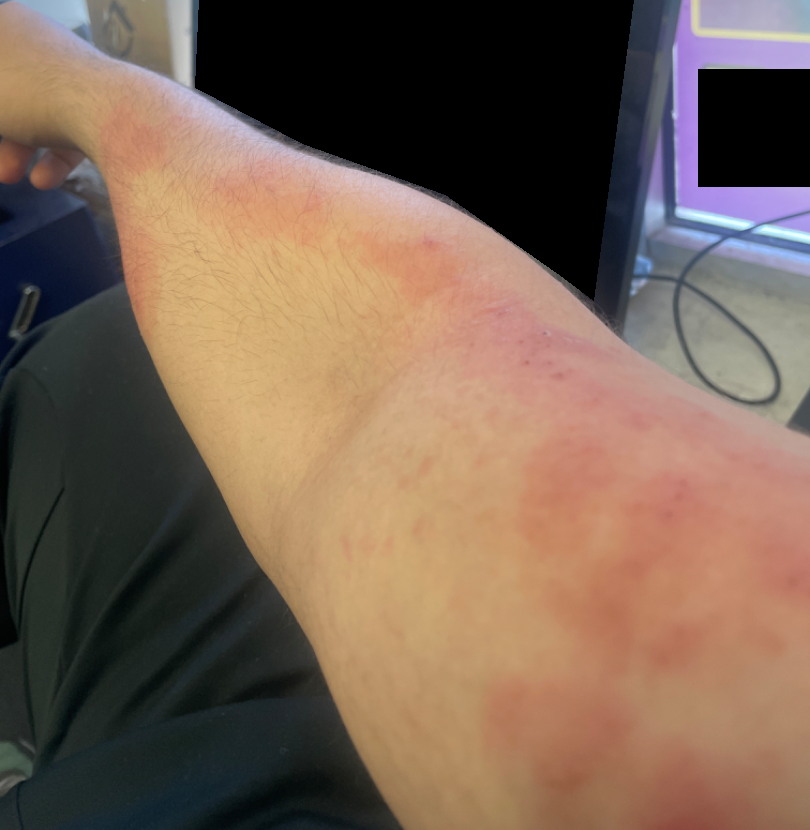body_site: arm
shot_type: at an angle
differential:
  Allergic Contact Dermatitis: 0.38
  Lichenified eczematous dermatitis: 0.25
  Eczema: 0.19
  Acute dermatitis, NOS: 0.19